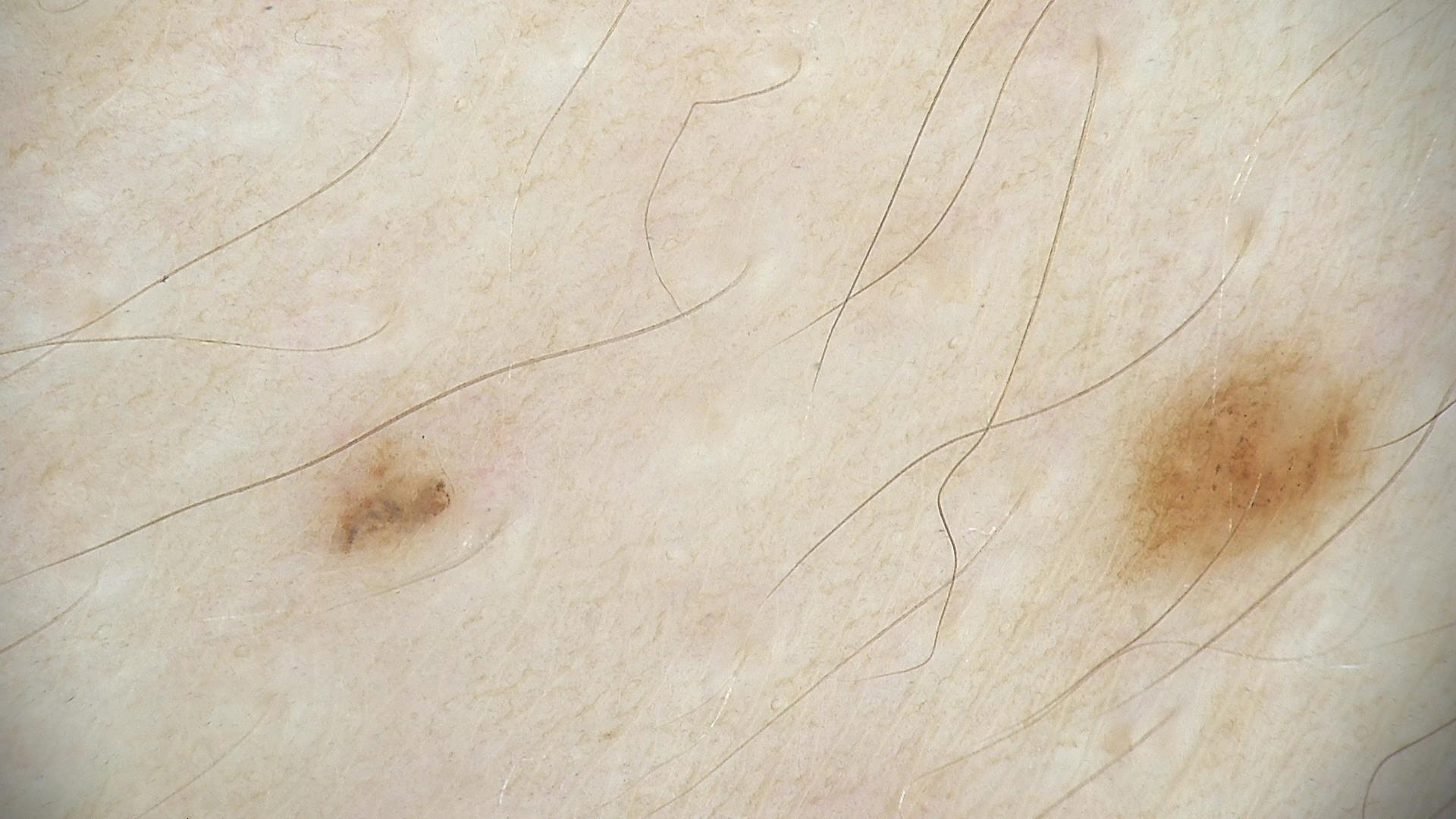Findings:
A skin lesion imaged with a dermatoscope.
Conclusion:
Classified as a dysplastic junctional nevus.